A dermoscopic photograph of a skin lesion:
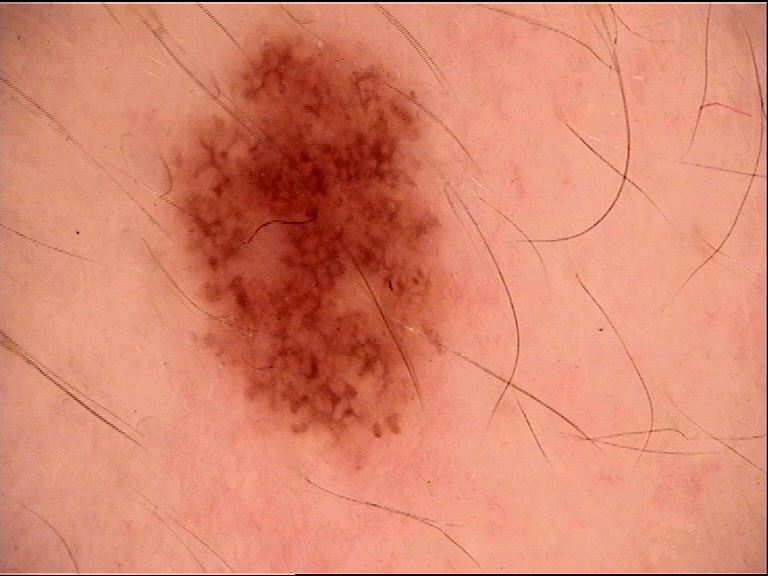Q: What is this lesion?
A: dysplastic junctional nevus (expert consensus)